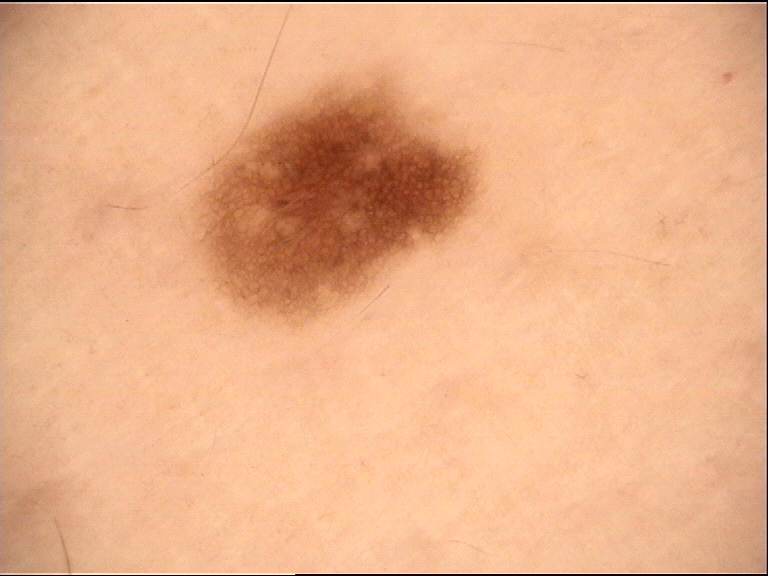Impression:
Labeled as a benign lesion — a dysplastic junctional nevus.